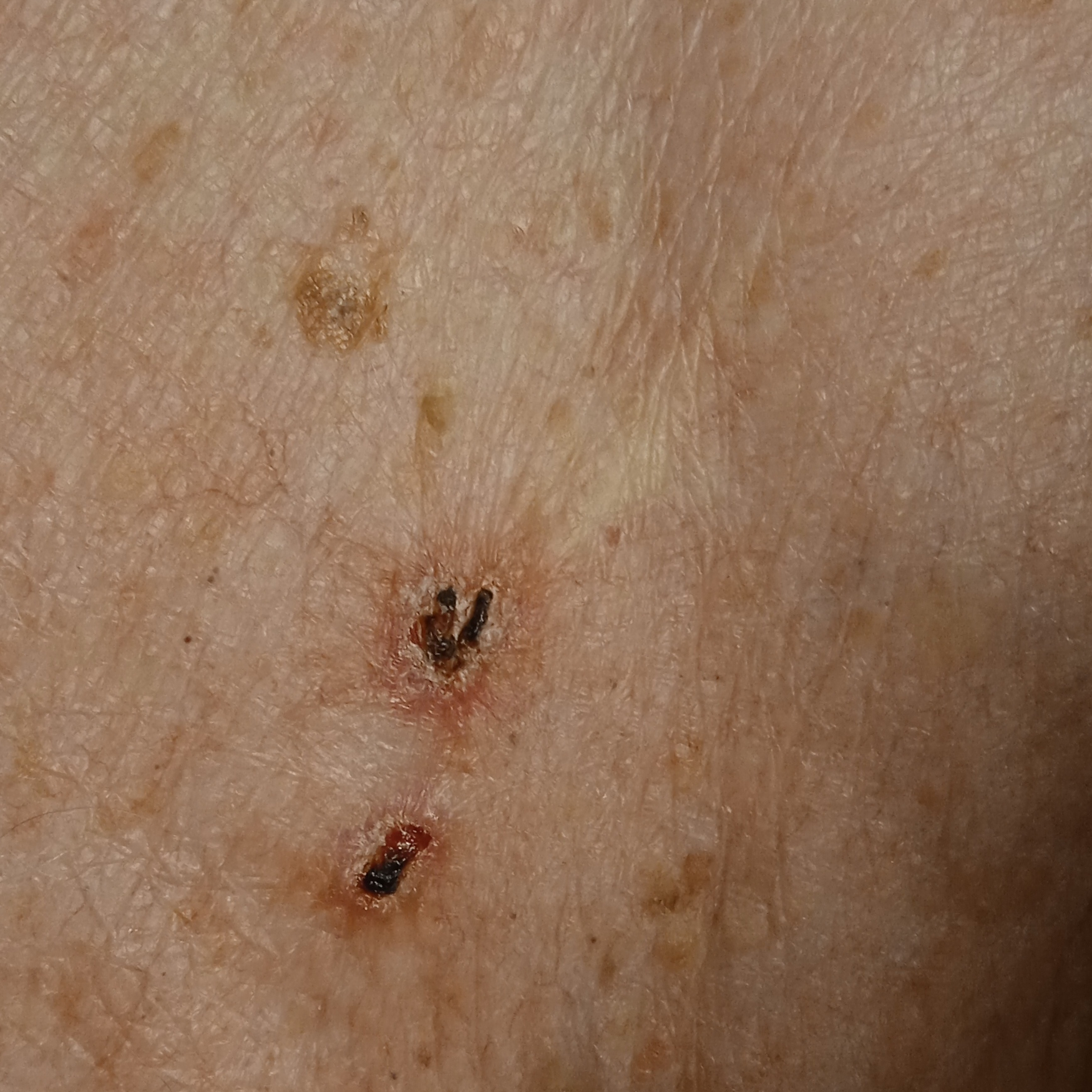<record>
<diagnosis>
<name>basal cell carcinoma</name>
<malignancy>malignant</malignancy>
</diagnosis>
</record>